Referred with a clinical suspicion of Bowen's disease. Dermoscopy of a skin lesion. By self-report, no personal history of cancer and no immunosuppression. A male subject 83 years of age:
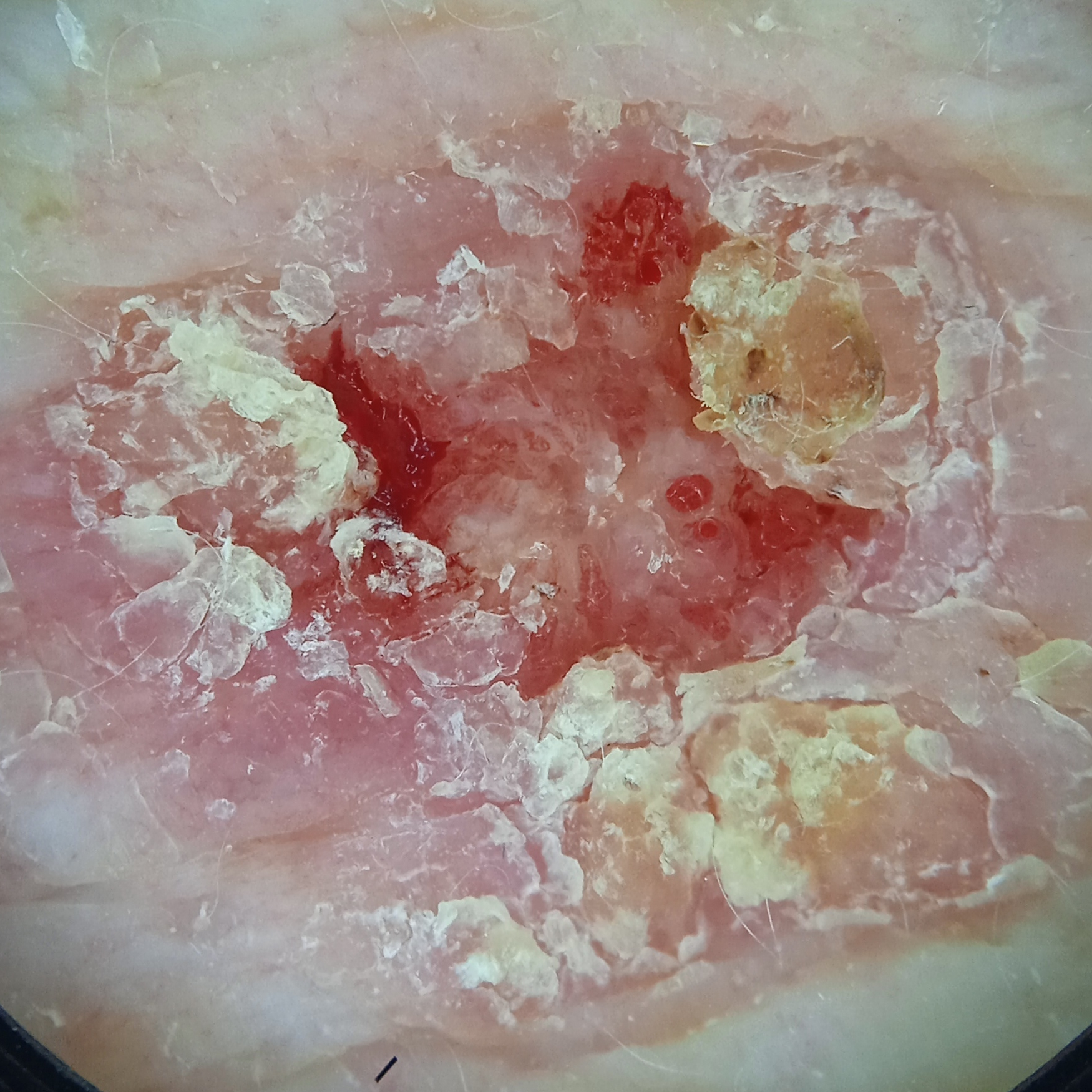Q: What is the anatomic site?
A: the torso
Q: Lesion size?
A: 14.5 mm
Q: What was the diagnosis?
A: squamous cell carcinoma (dermatologist consensus)